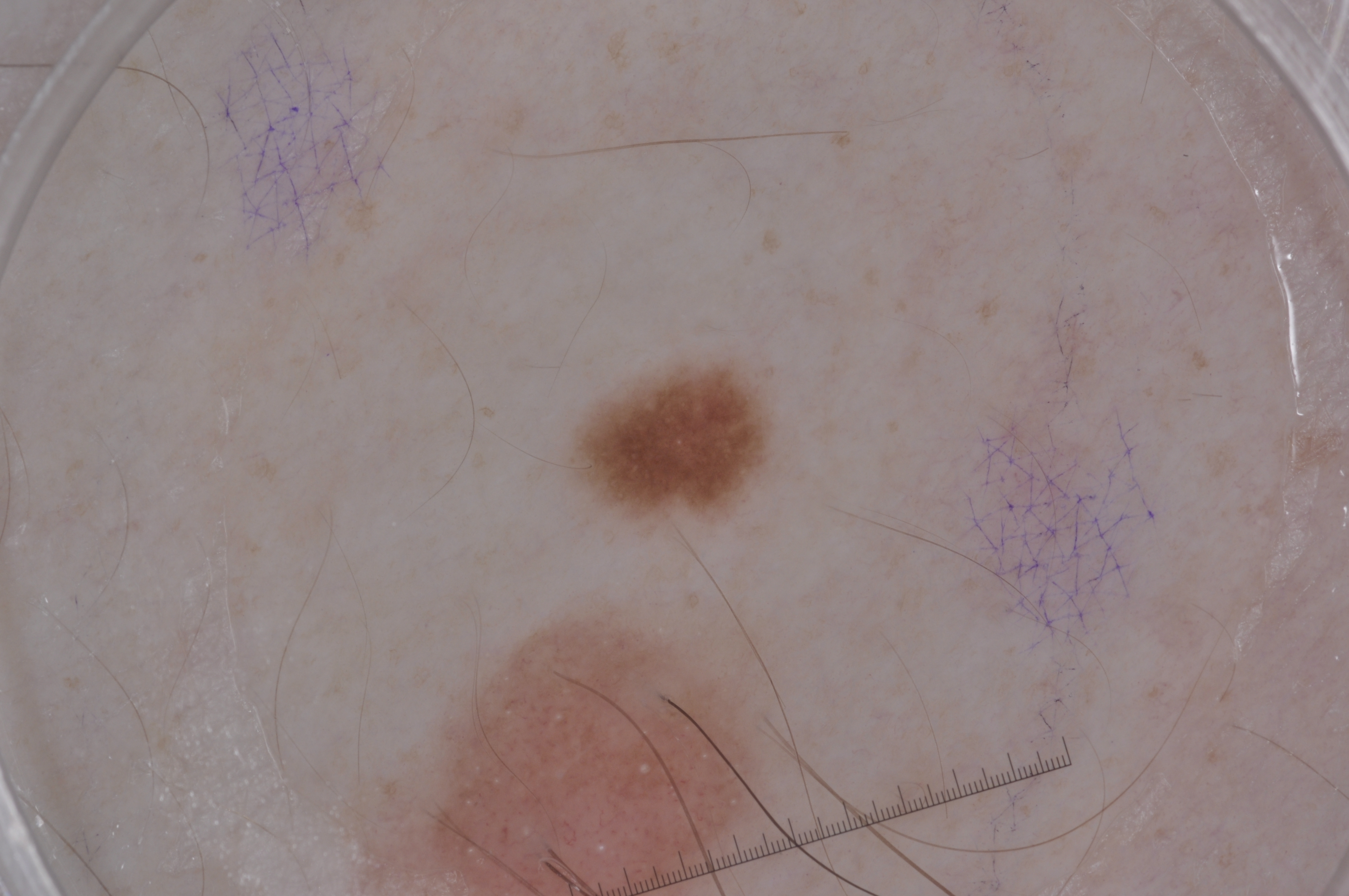patient = male, in their mid-20s | image = dermoscopic image | dermoscopic findings = milia-like cysts; absent: streaks, negative network, and pigment network | bounding box = left=567, top=360, right=772, bottom=523 | diagnostic label = a melanocytic nevus, a benign lesion.